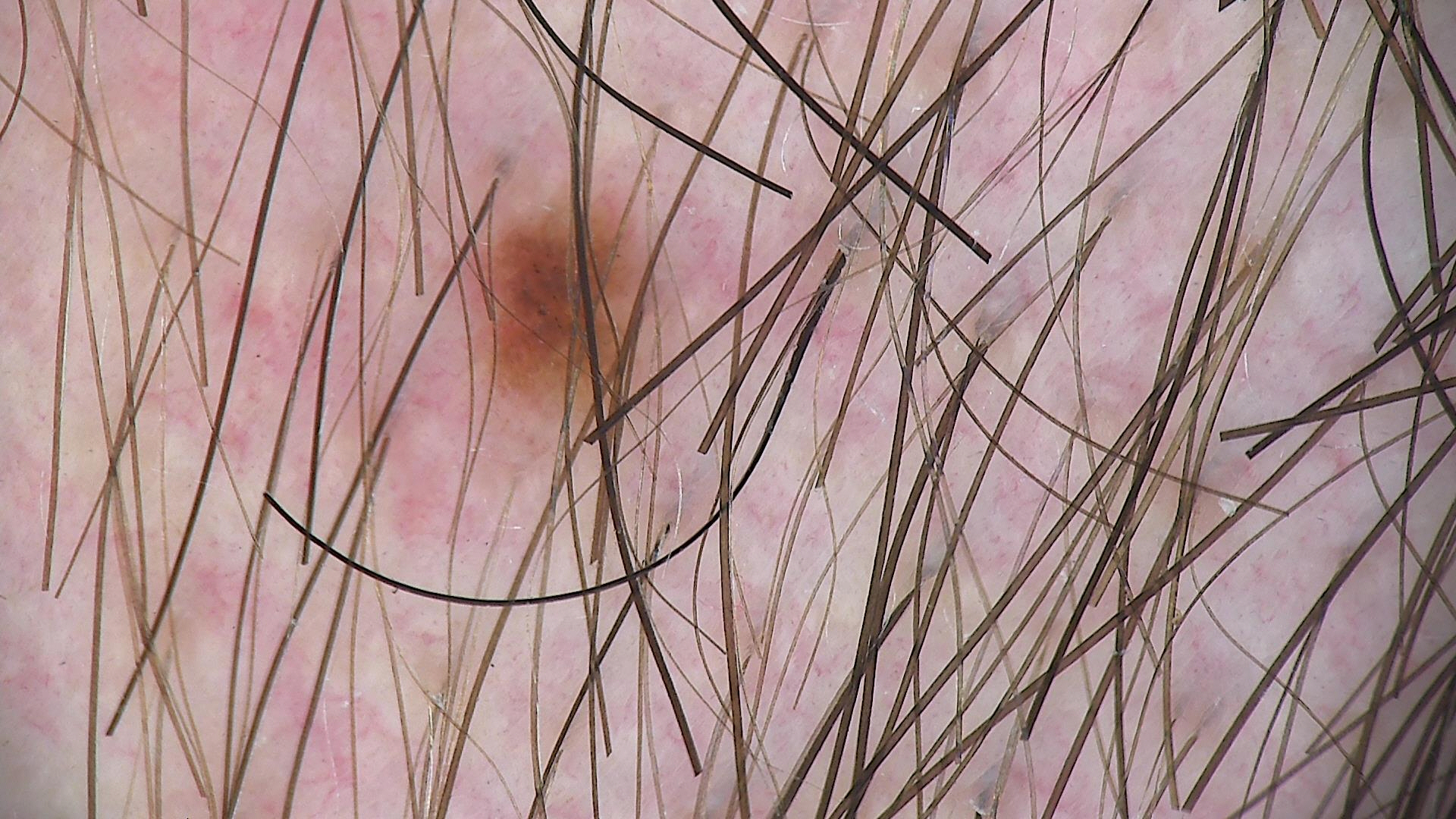Classified as a dysplastic junctional nevus.